A dermoscopic photograph of a skin lesion:
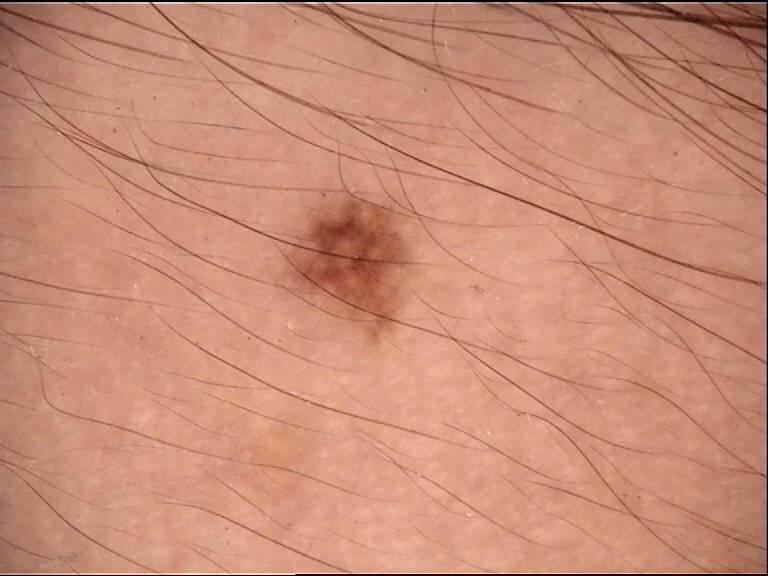The architecture is that of a compound, banal lesion. Classified as a Miescher nevus.